A close-up photograph; self-categorized by the patient as a rash; texture is reported as raised or bumpy; the affected area is the head or neck, arm, leg and top or side of the foot; the lesion is associated with bothersome appearance:
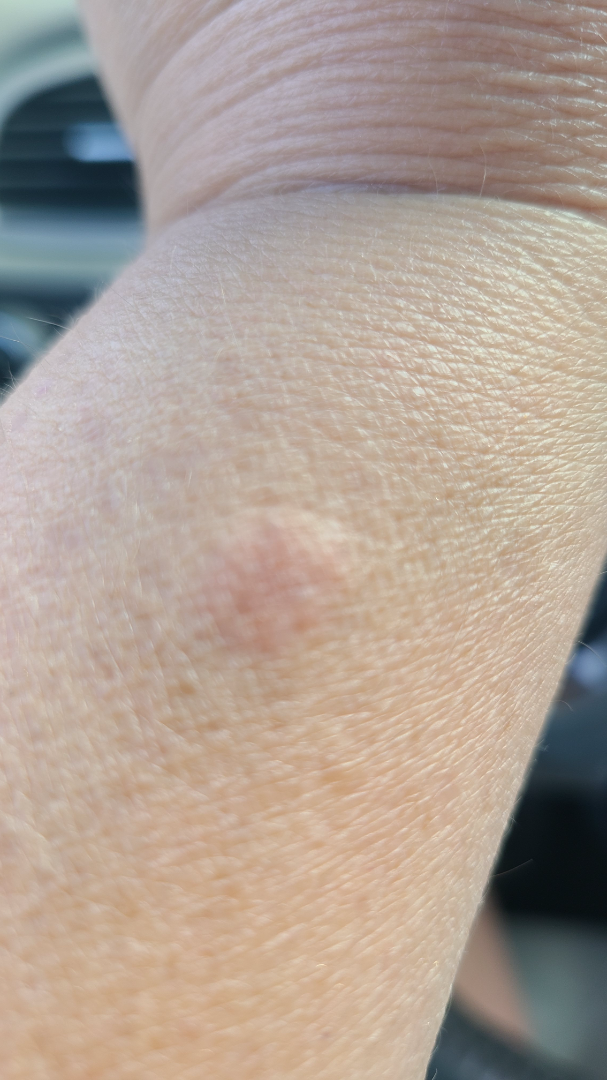The skin findings could not be characterized from the image.